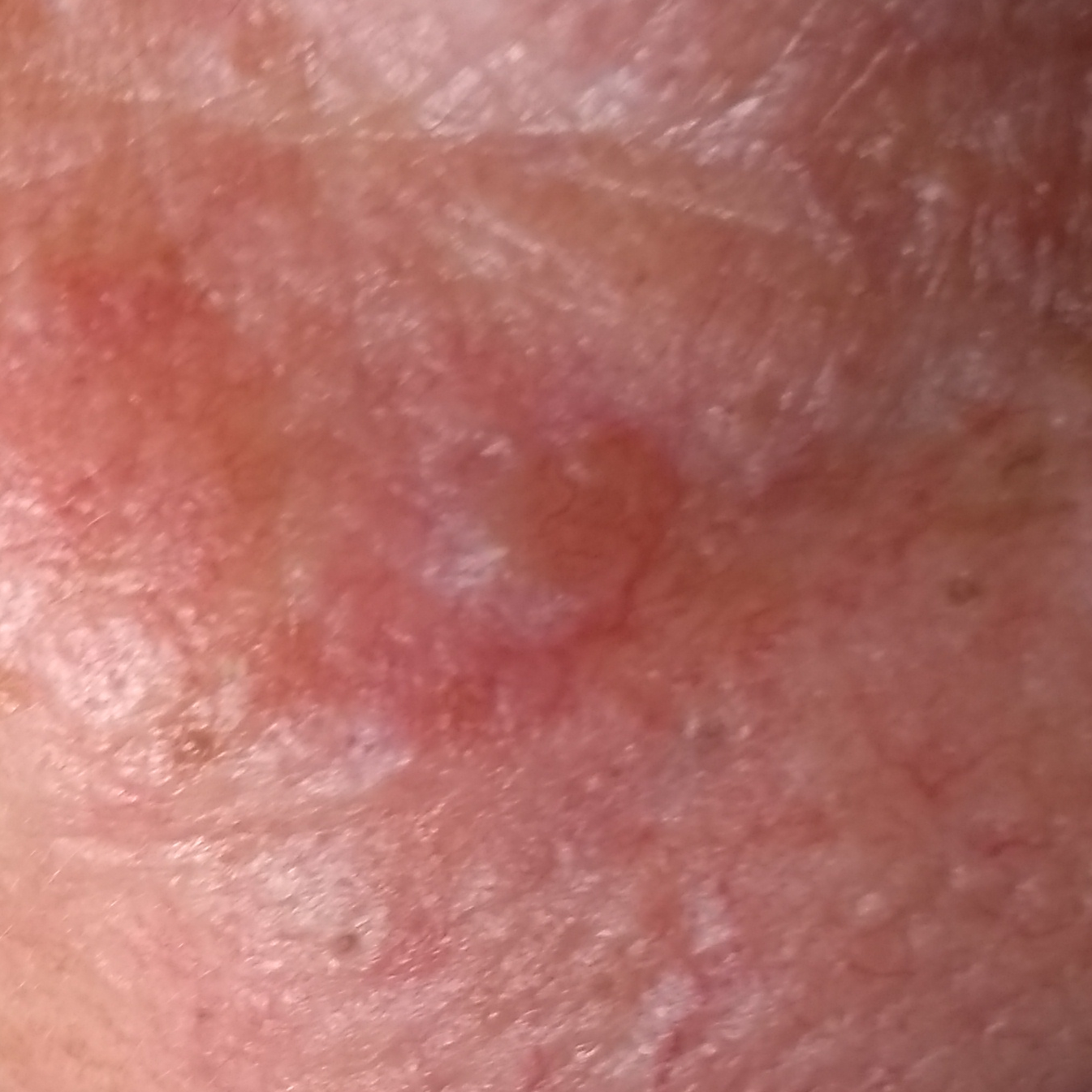{"skin_type": "II", "image": "clinical photo", "patient": {"age": 77, "gender": "female"}, "risk_factors": {"positive": ["prior cancer (patient or family)", "prior skin cancer (patient or family)"]}, "lesion_size": {"diameter_1_mm": 10.0, "diameter_2_mm": 8.0}, "diagnosis": {"name": "basal cell carcinoma", "code": "BCC", "malignancy": "malignant", "confirmation": "histopathology"}}